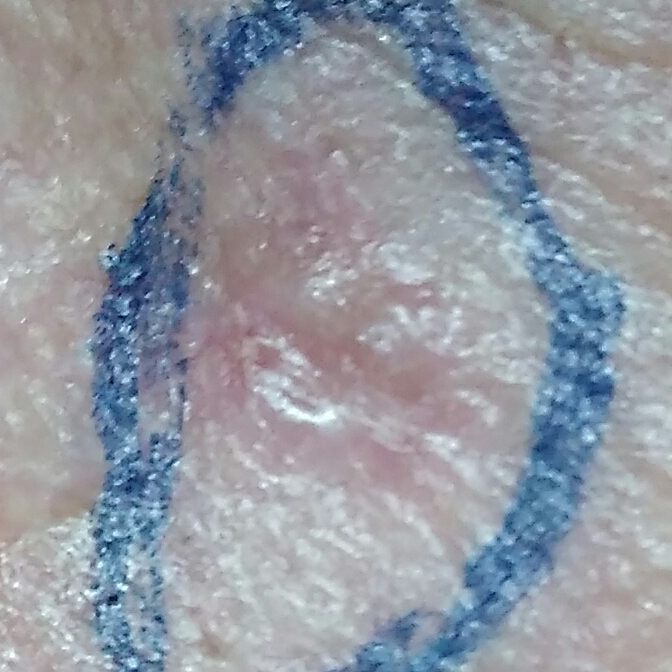Q: Skin phototype?
A: III
Q: What does the exposure history note?
A: prior malignancy (patient or family), pesticide exposure, tobacco use, prior skin cancer (patient or family), alcohol use
Q: What kind of image is this?
A: smartphone clinical photo
Q: Who is the patient?
A: male, age 64
Q: What is the anatomic site?
A: the face
Q: Lesion size?
A: 7 × 6 mm
Q: Any reported symptoms?
A: elevation, growth / no itching
Q: What is this lesion?
A: basal cell carcinoma (biopsy-proven)